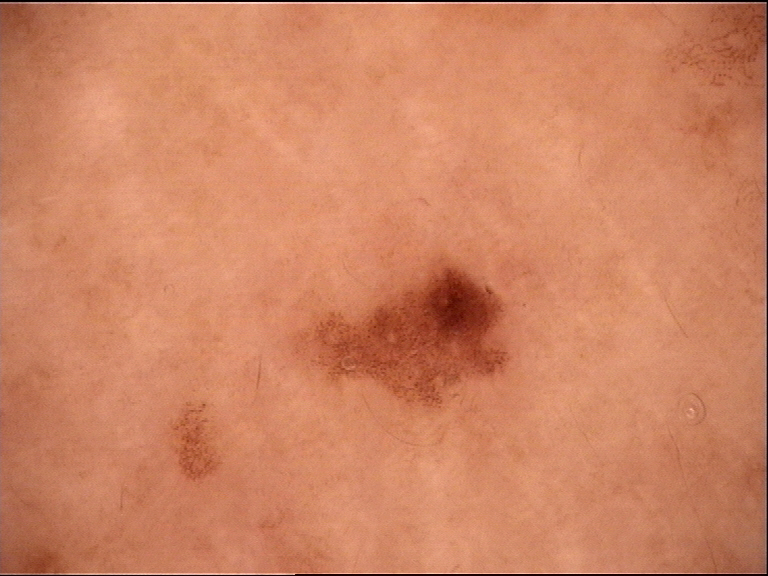image: dermatoscopy; diagnosis: dysplastic junctional nevus (expert consensus).